A dermoscopy image of a single skin lesion:
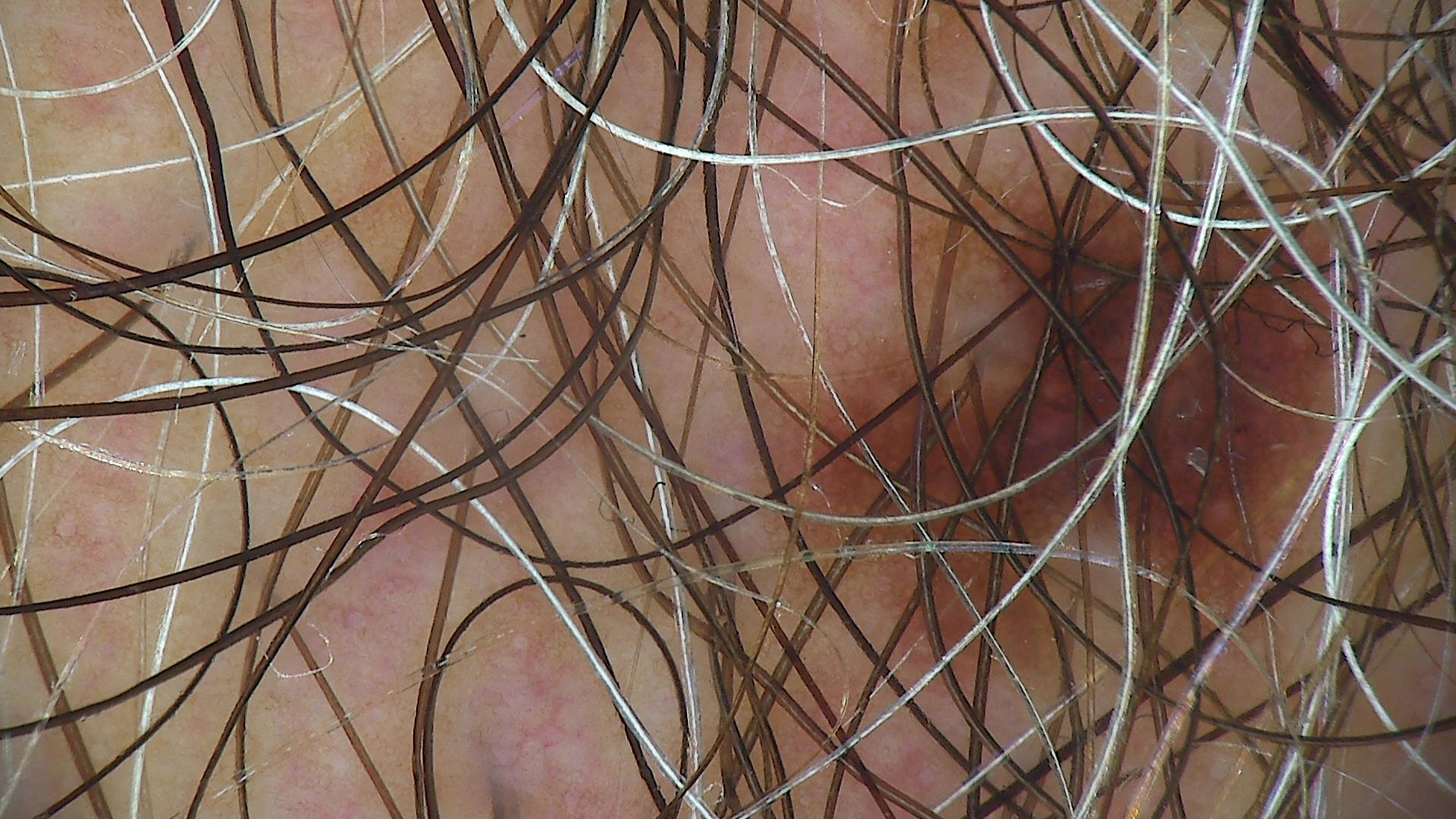assessment: dysplastic junctional nevus (expert consensus).